Close-up view — 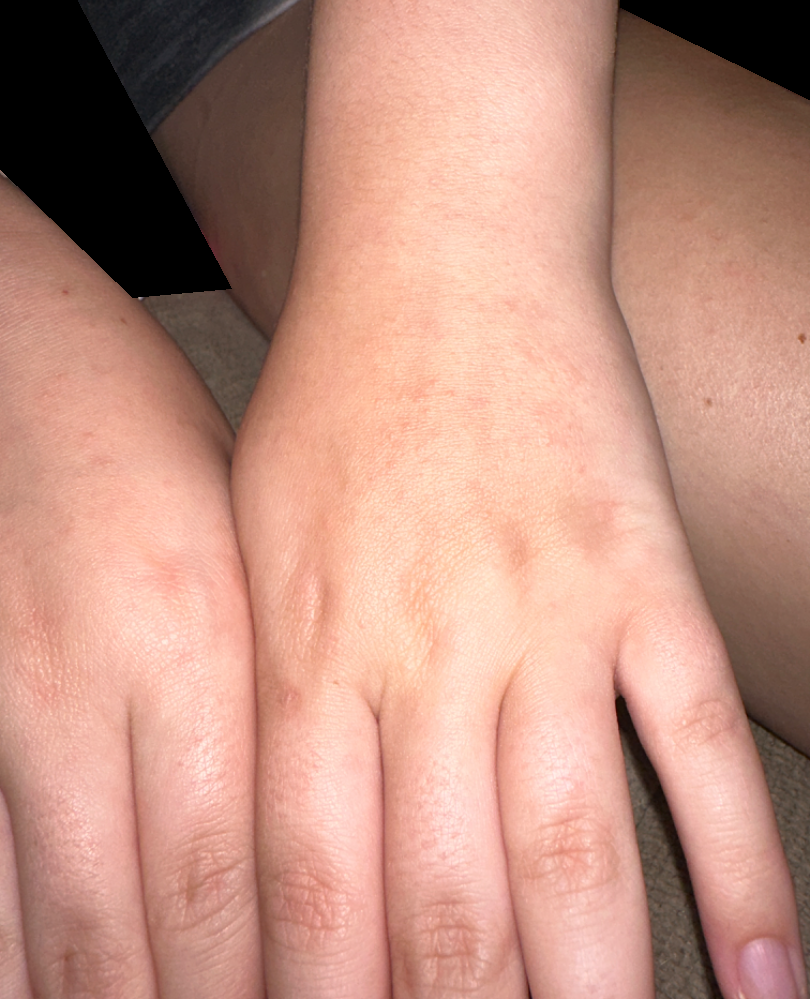- assessment · no findings on review